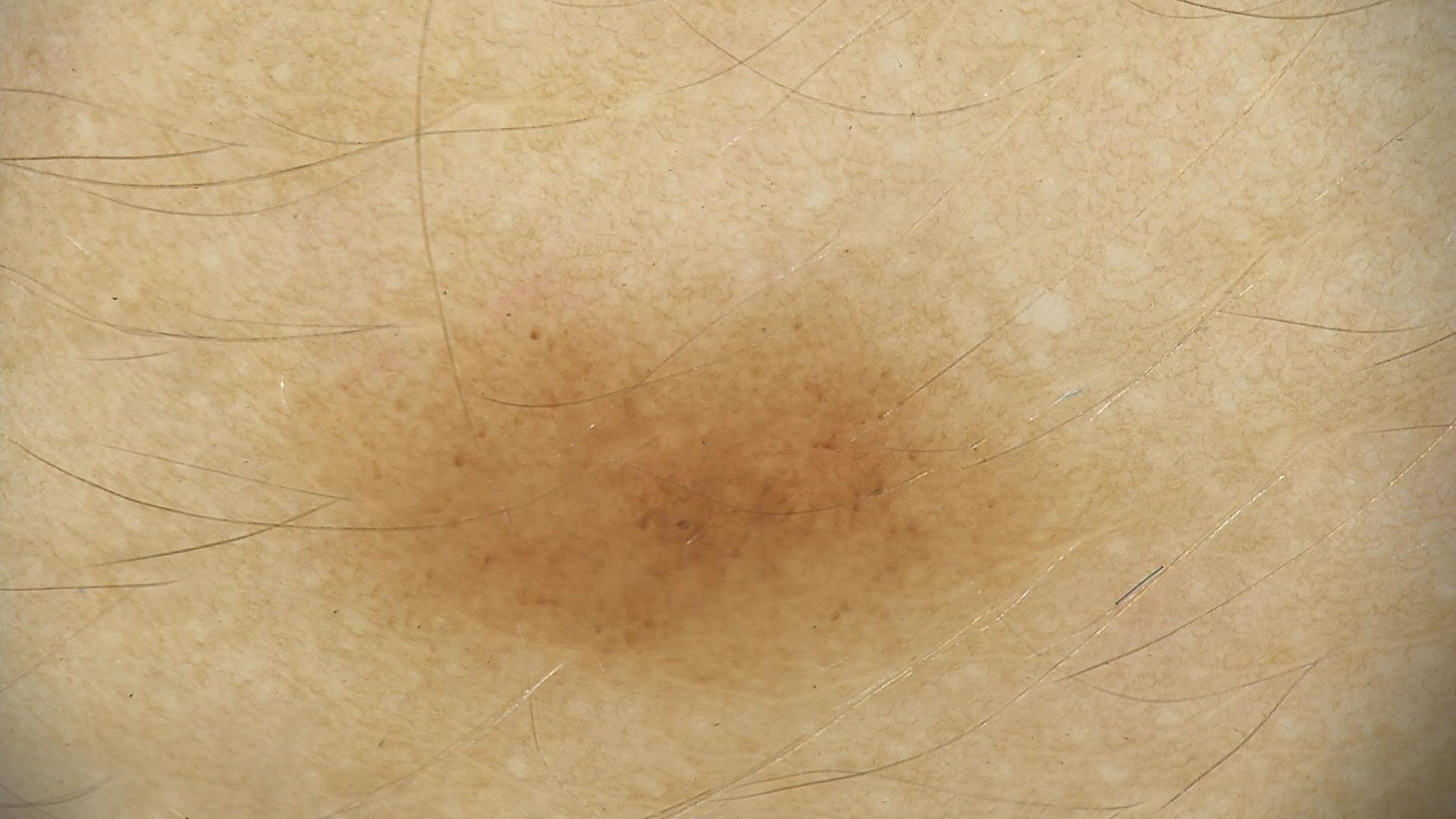<dermoscopy>
  <image>dermatoscopy</image>
  <diagnosis>
    <name>dysplastic junctional nevus</name>
    <code>jd</code>
    <malignancy>benign</malignancy>
    <super_class>melanocytic</super_class>
    <confirmation>expert consensus</confirmation>
  </diagnosis>
</dermoscopy>